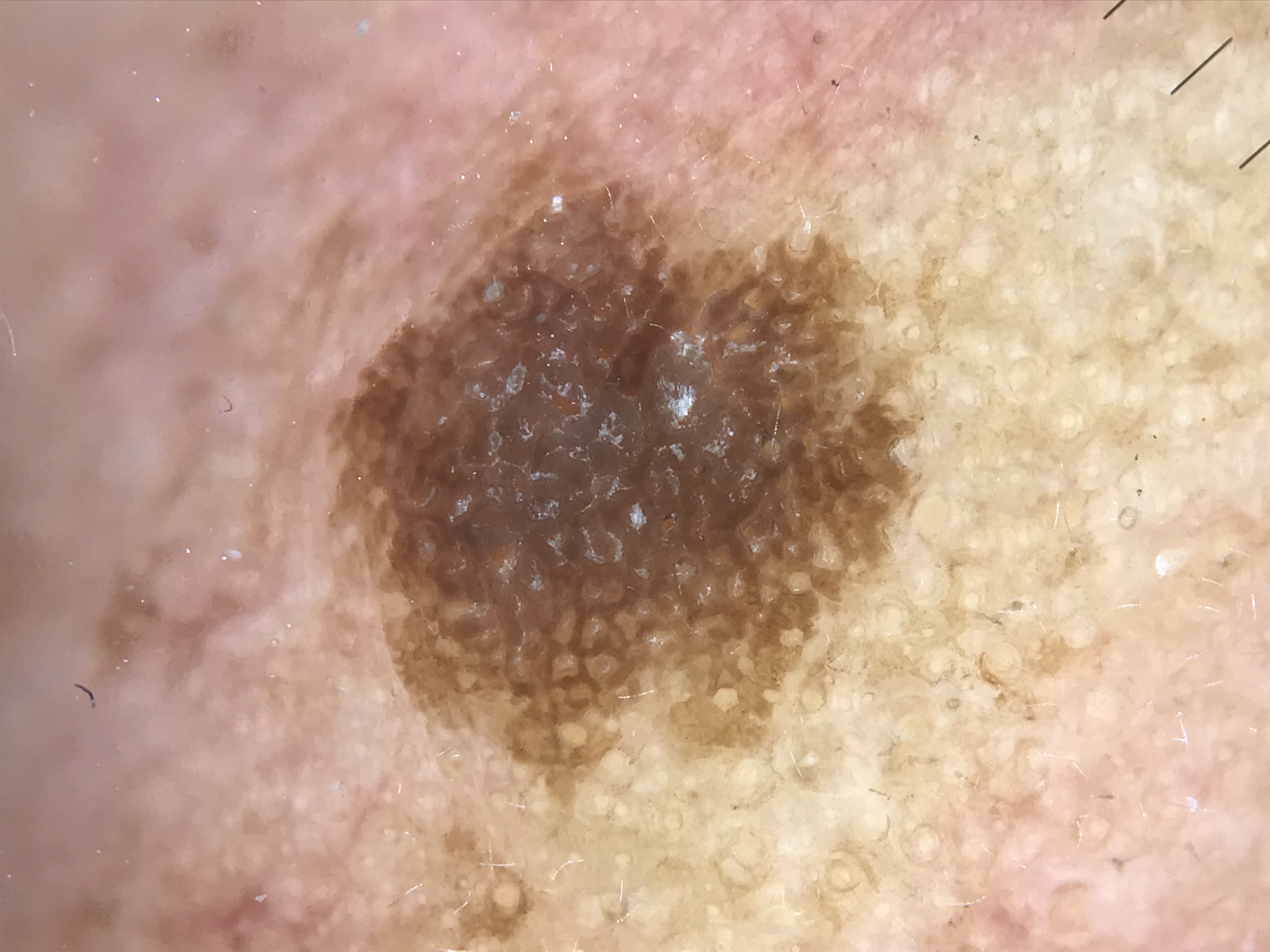Q: What is the imaging modality?
A: dermoscopy
Q: What kind of lesion is this?
A: keratinocytic
Q: What is this lesion?
A: seborrheic keratosis (expert consensus)